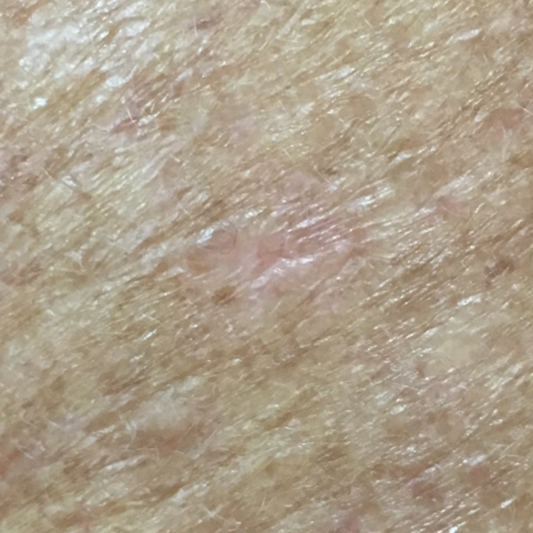subject — female, 66 years old; FST — II; risk factors — prior skin cancer (patient or family), prior malignancy (patient or family), alcohol use, no pesticide exposure; region — a hand; pathology — basal cell carcinoma (biopsy-proven).